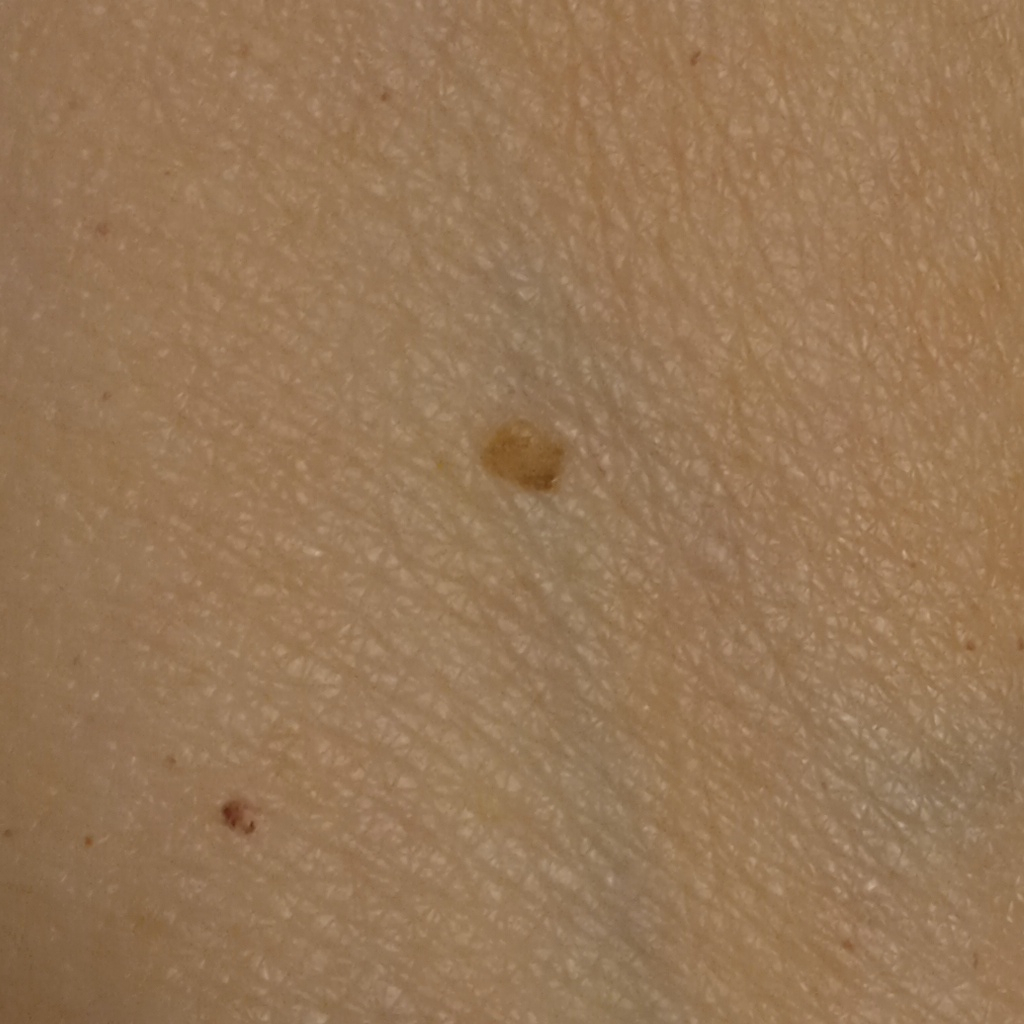{"image": "clinical photo", "referral": "research study (no referral diagnosis)", "patient": {"age": 67, "sex": "female"}, "lesion_location": "an arm", "diagnosis": {"name": "seborrheic keratosis", "malignancy": "benign"}}